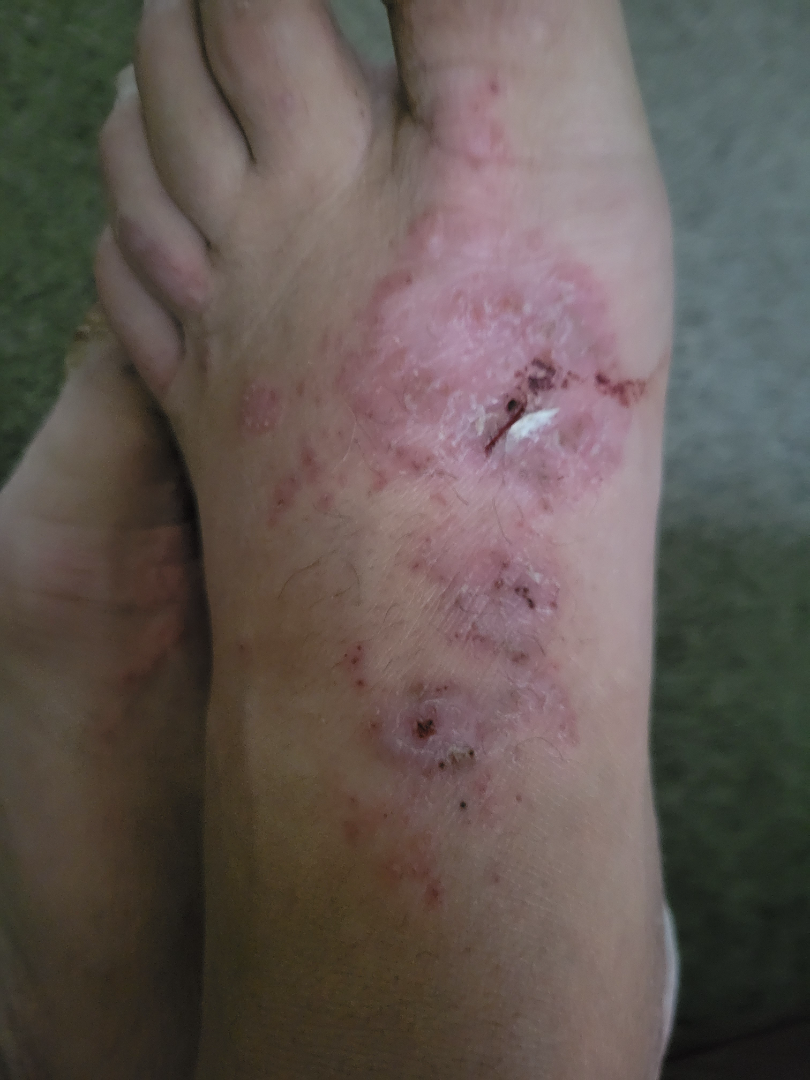Patient information:
The patient described the issue as a rash. The photograph is a close-up of the affected area. The lesion involves the top or side of the foot. Fitzpatrick phototype III; human graders estimated Monk skin tone scale 2. No relevant systemic symptoms.
Review:
On remote dermatologist review: Tinea (favored); Eczema (considered); Psoriasis (considered).